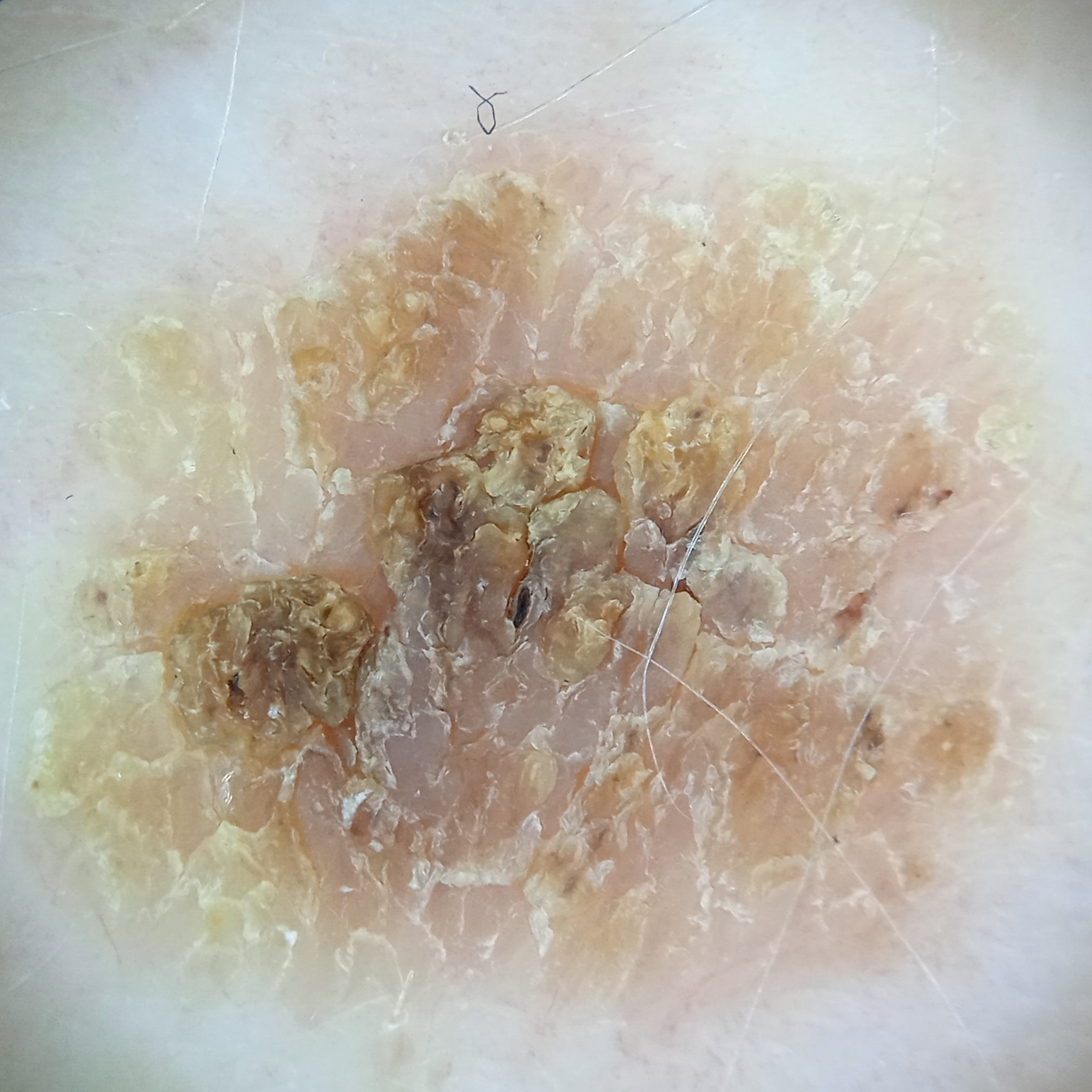patient = male, age 78 | nevus count = few melanocytic nevi overall | clinical context = research study (no referral diagnosis) | image = dermoscopic image | sun reaction = skin reddens with sun exposure | anatomic site = the back | size = 11 mm | diagnostic label = seborrheic keratosis (dermatologist consensus).